An image taken at an angle — 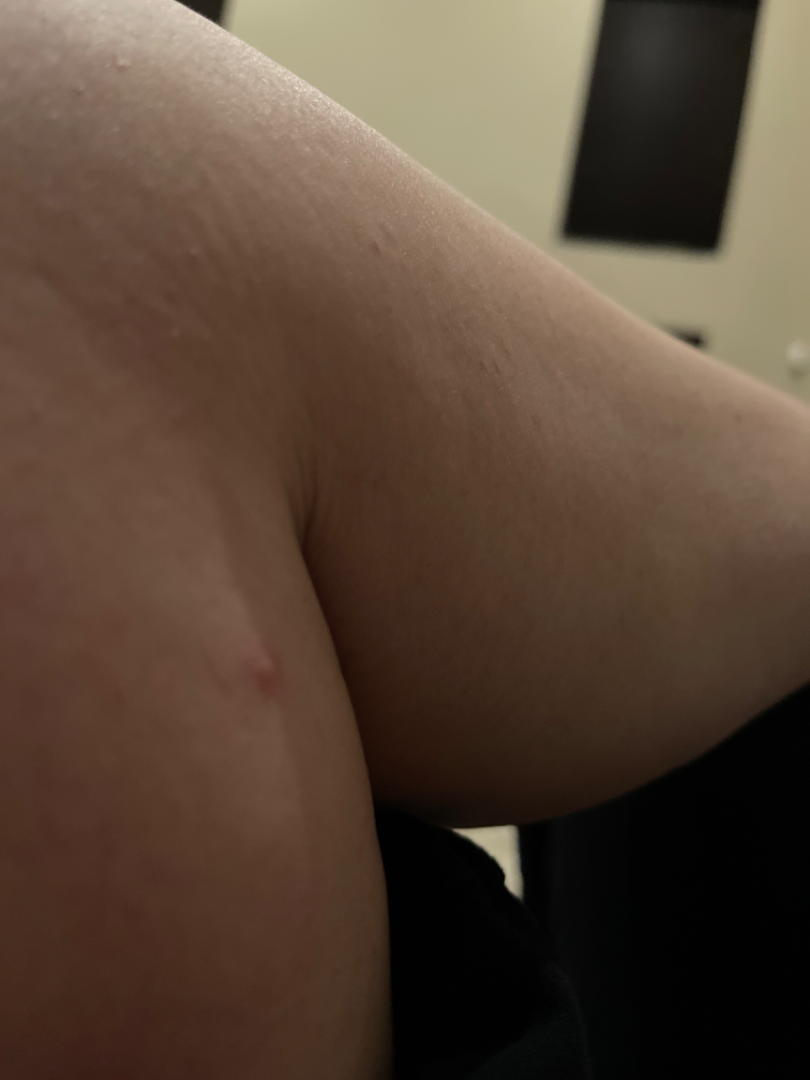Impression: The reviewer was unable to grade this case for skin condition.